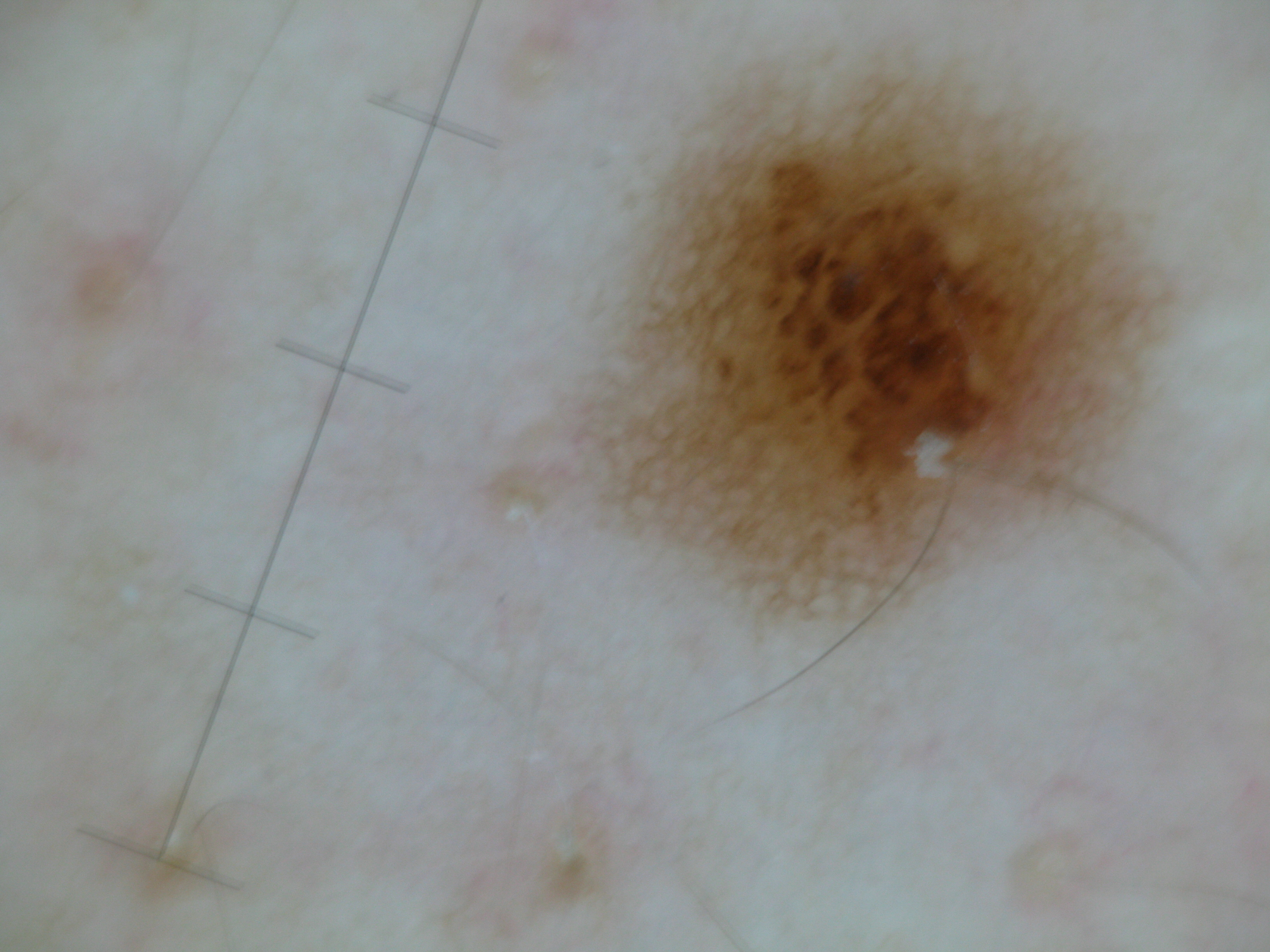| key | value |
|---|---|
| imaging | dermatoscopy |
| category | banal |
| diagnosis | compound nevus (expert consensus) |